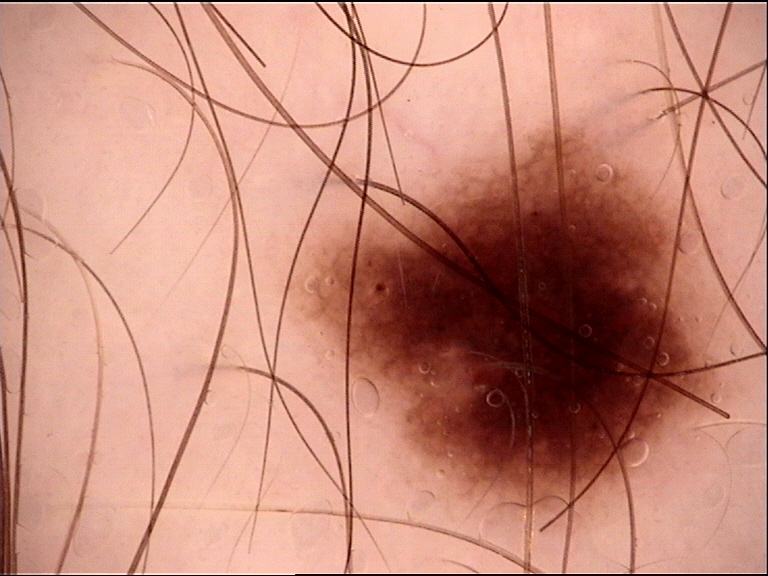A dermatoscopic image of a skin lesion.
The diagnostic label was a benign lesion — a dysplastic junctional nevus.